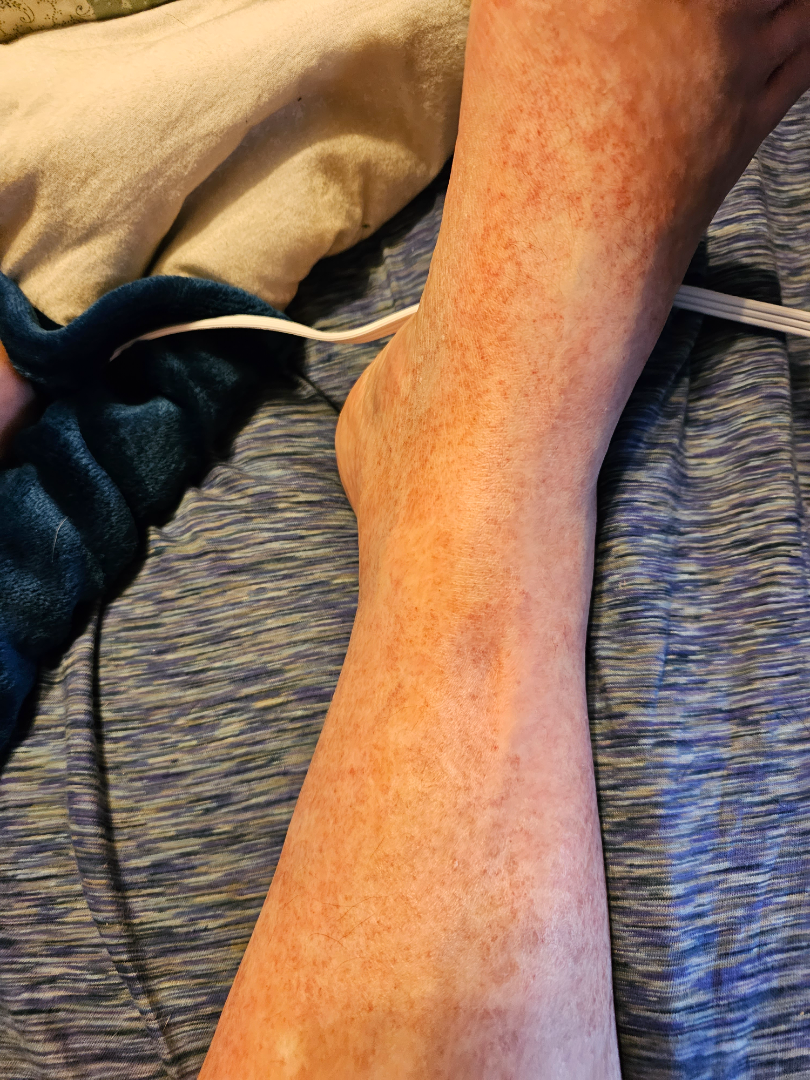skin tone = non-clinician graders estimated MST 3 or 4 | present for = one to four weeks | texture = flat | patient's own categorization = a rash | contributor = male, age 60–69 | lesion symptoms = bothersome appearance | affected area = leg | view = close-up | dermatologist impression = most likely Pigmented purpuric eruption; also on the differential is Stasis Dermatitis; also consider Leukocytoclastic Vasculitis.